The lesion involves the leg; an image taken at an angle; the subject is a female aged 50–59: 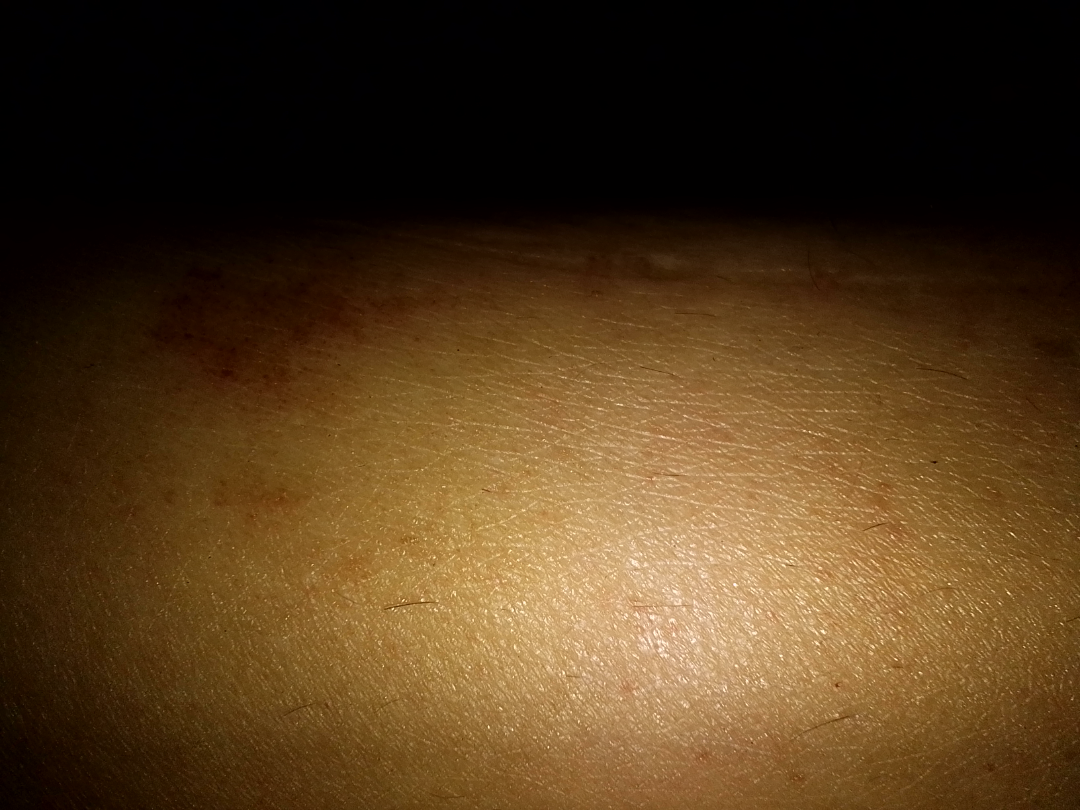History: Texture is reported as flat. Self-categorized by the patient as skin that appeared healthy to them. The lesion is associated with pain, itching and burning. Impression: Three independent reviewers: in keeping with Pigmented purpuric eruption.